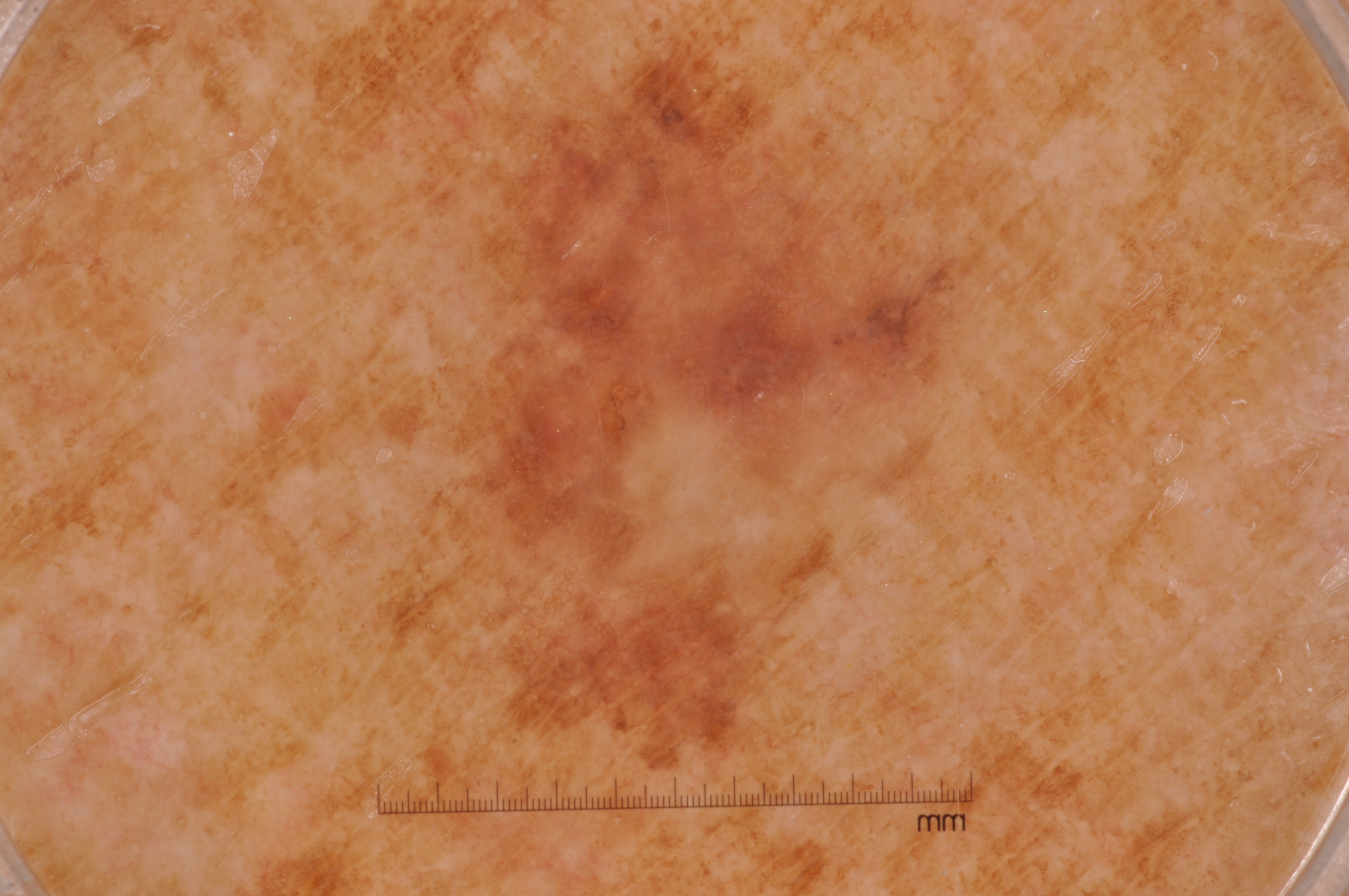Notes:
* patient · female, roughly 55 years of age
* image · dermoscopy of a skin lesion
* lesion extent · moderate
* bounding box · bbox(433, 28, 959, 749)
* dermoscopic features · pigment network and milia-like cysts; absent: streaks and negative network
* impression · a melanoma, a skin cancer